A dermoscopic image of a skin lesion:
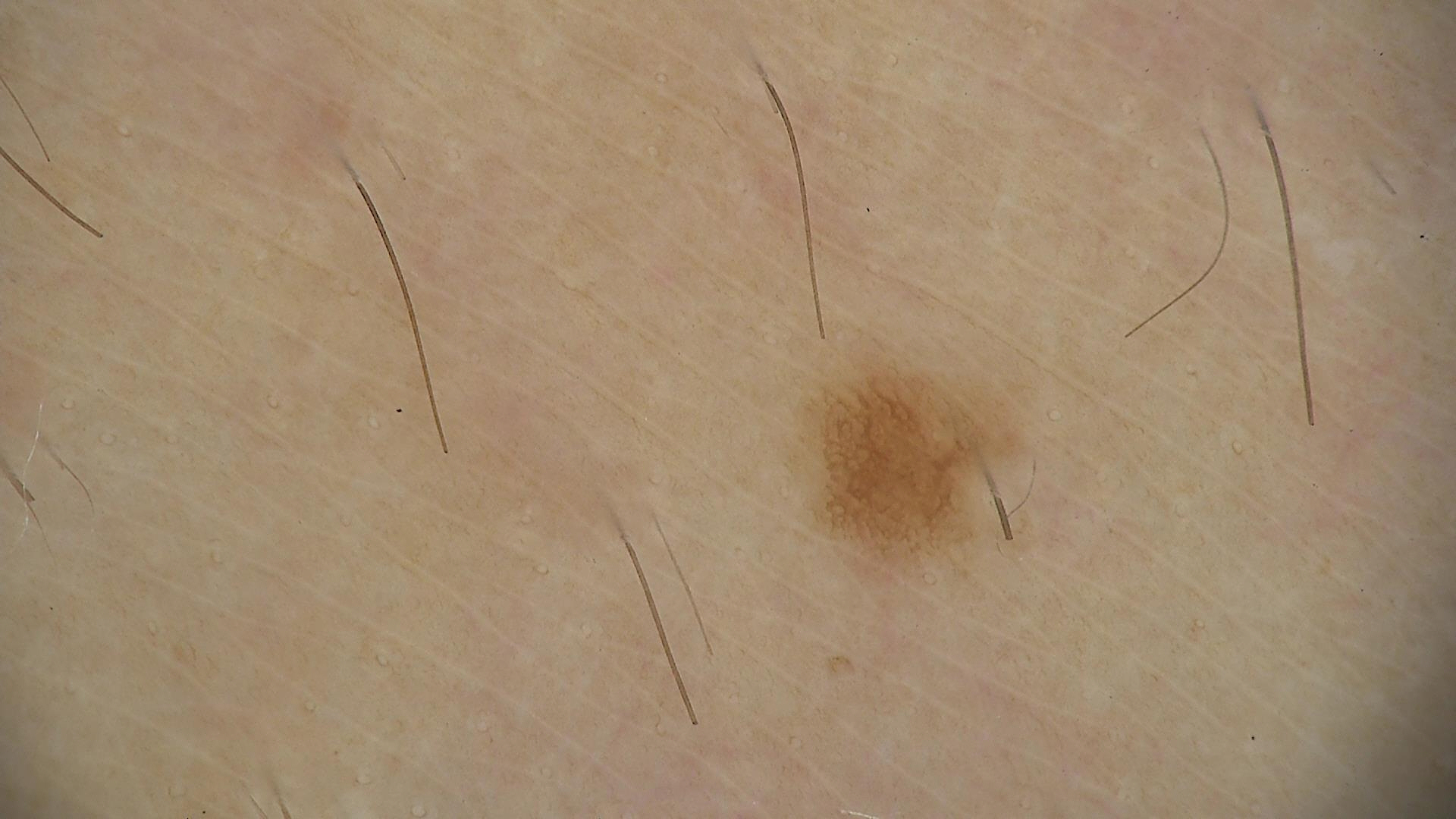label = junctional nevus (expert consensus)